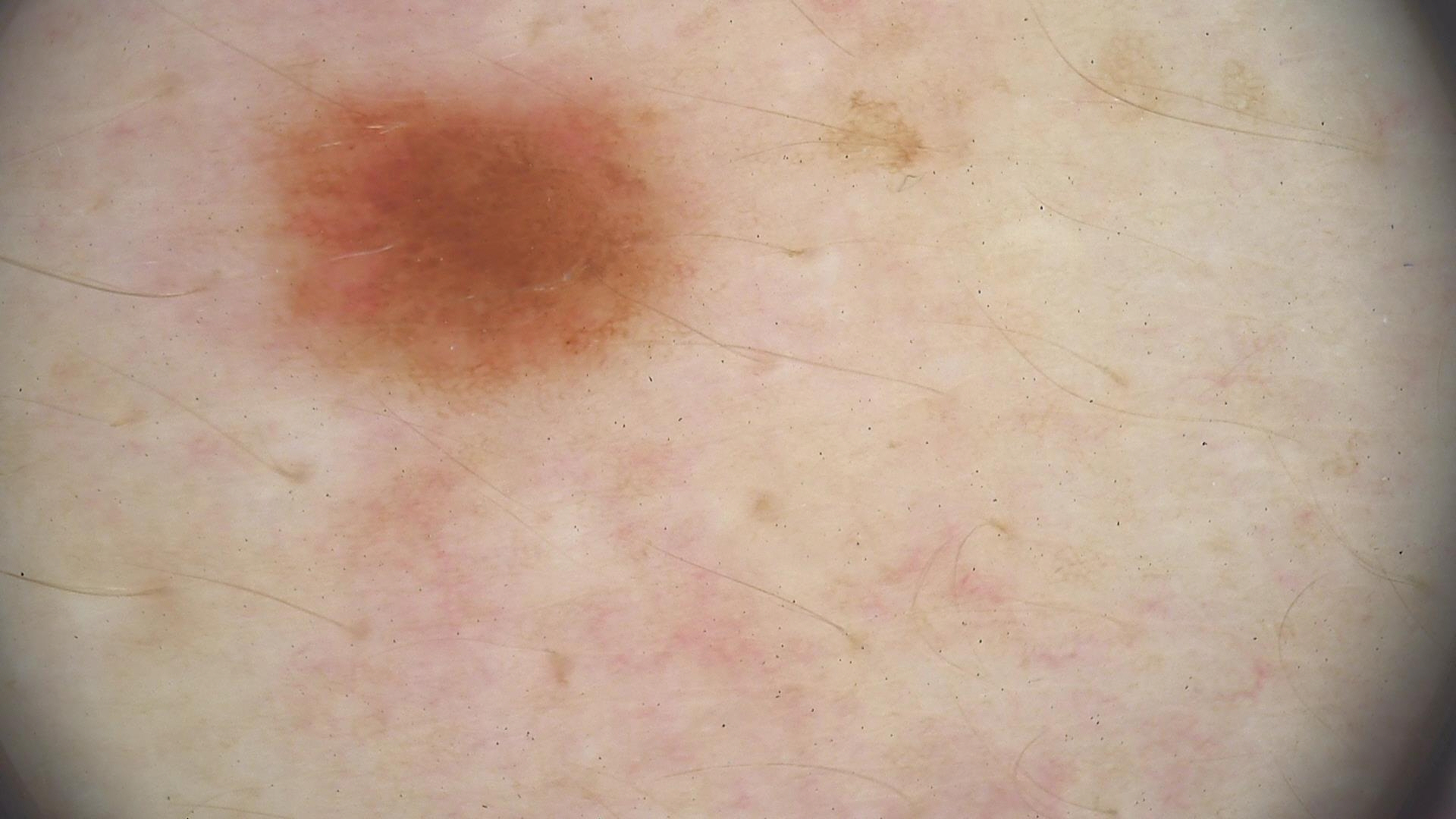| feature | finding |
|---|---|
| modality | dermatoscopy |
| label | dysplastic compound nevus (expert consensus) |